A clinical photograph showing a skin lesion in context · the chart notes a prior melanoma · a male subject about 40 years old · the patient was assessed as Fitzpatrick skin type II: 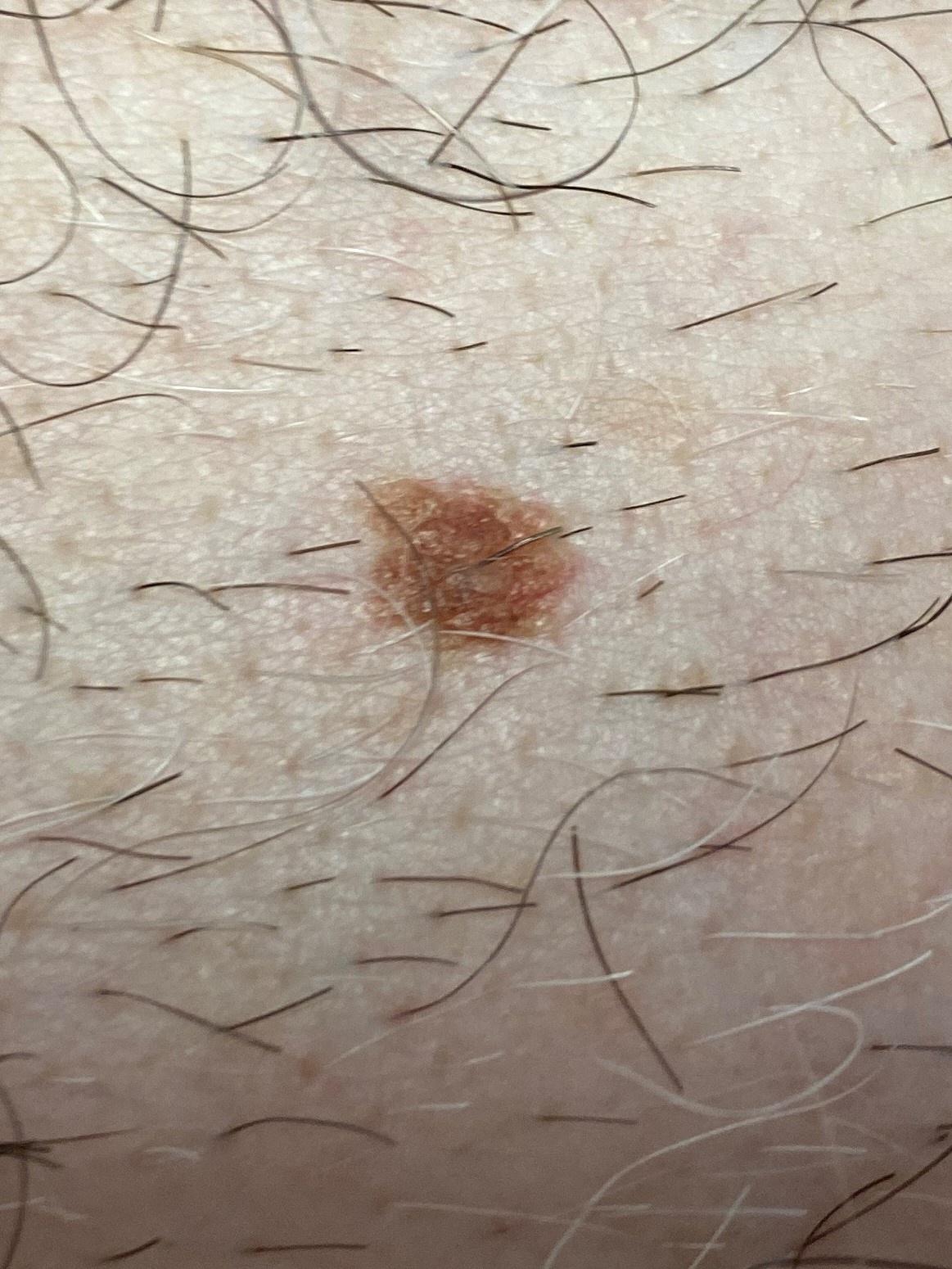Findings: The lesion was found on the trunk. Conclusion: Histopathology confirmed a benign lesion — a nevus.